The chart notes prior skin cancer (patient or family). A clinical photograph showing a skin lesion. The patient was assessed as Fitzpatrick phototype II. A female patient in their early 50s.
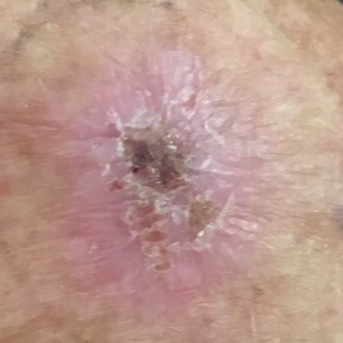Case summary: The lesion involves a forearm. The lesion measures 20 × 15 mm. The patient reports that the lesion hurts, itches, is elevated, has grown, and has bled. Diagnosis: Biopsy-confirmed as an actinic keratosis.